Dermoscopy of a skin lesion: 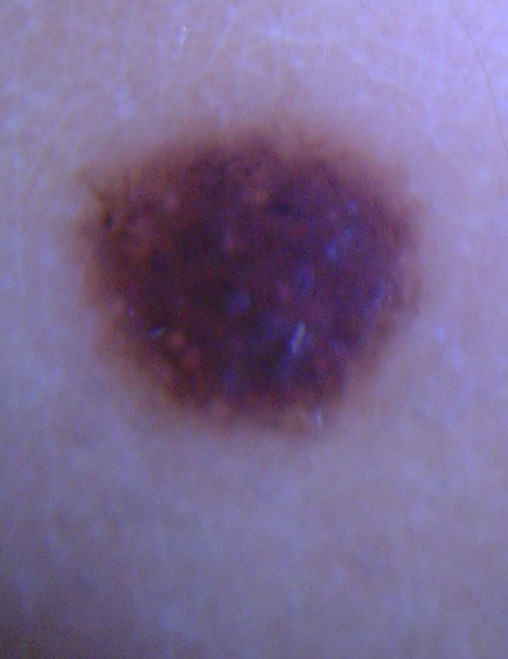  diagnosis:
    name: dysplastic compound nevus
    code: cd
    malignancy: benign
    super_class: melanocytic
    confirmation: expert consensus